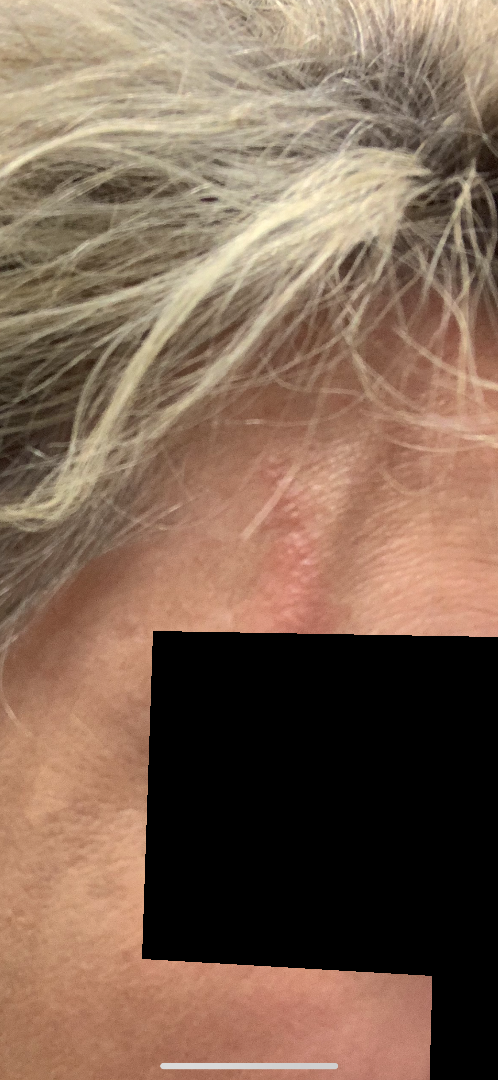The reviewer was unable to grade this case for skin condition.
The affected area is the head or neck.
The photo was captured at an angle.
Female subject, age 50–59.